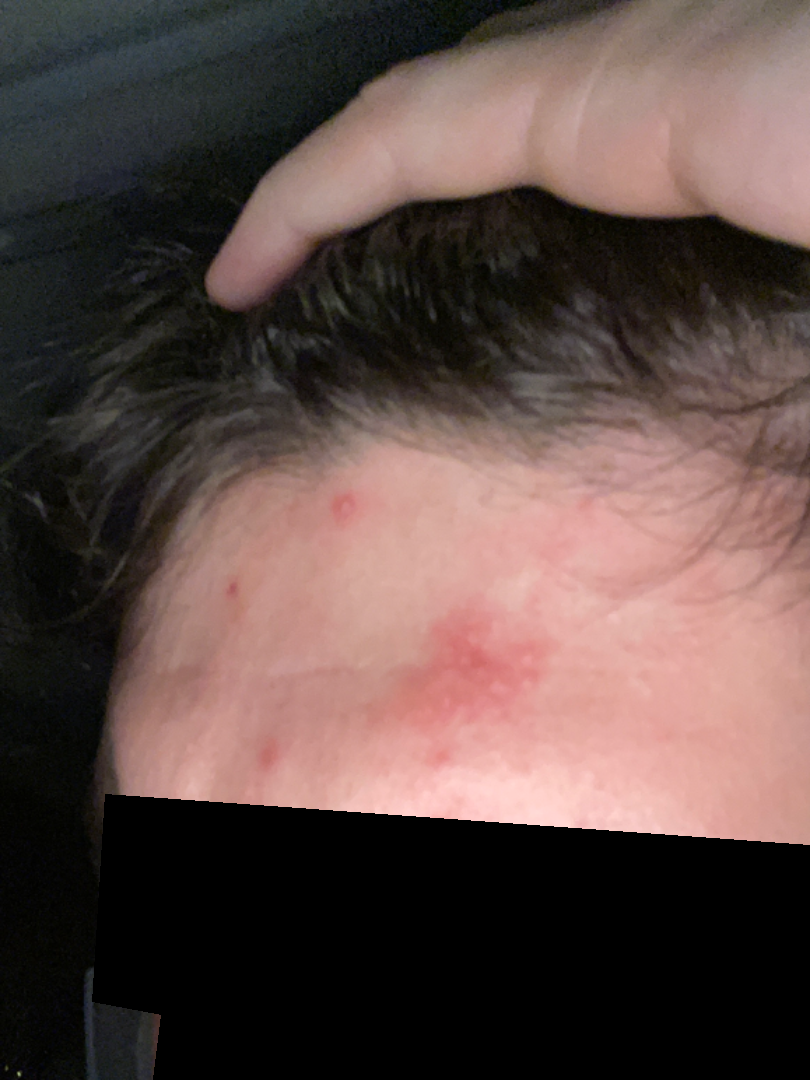Findings:
The condition could not be reliably identified from the image.